A dermoscopic image of a skin lesion: 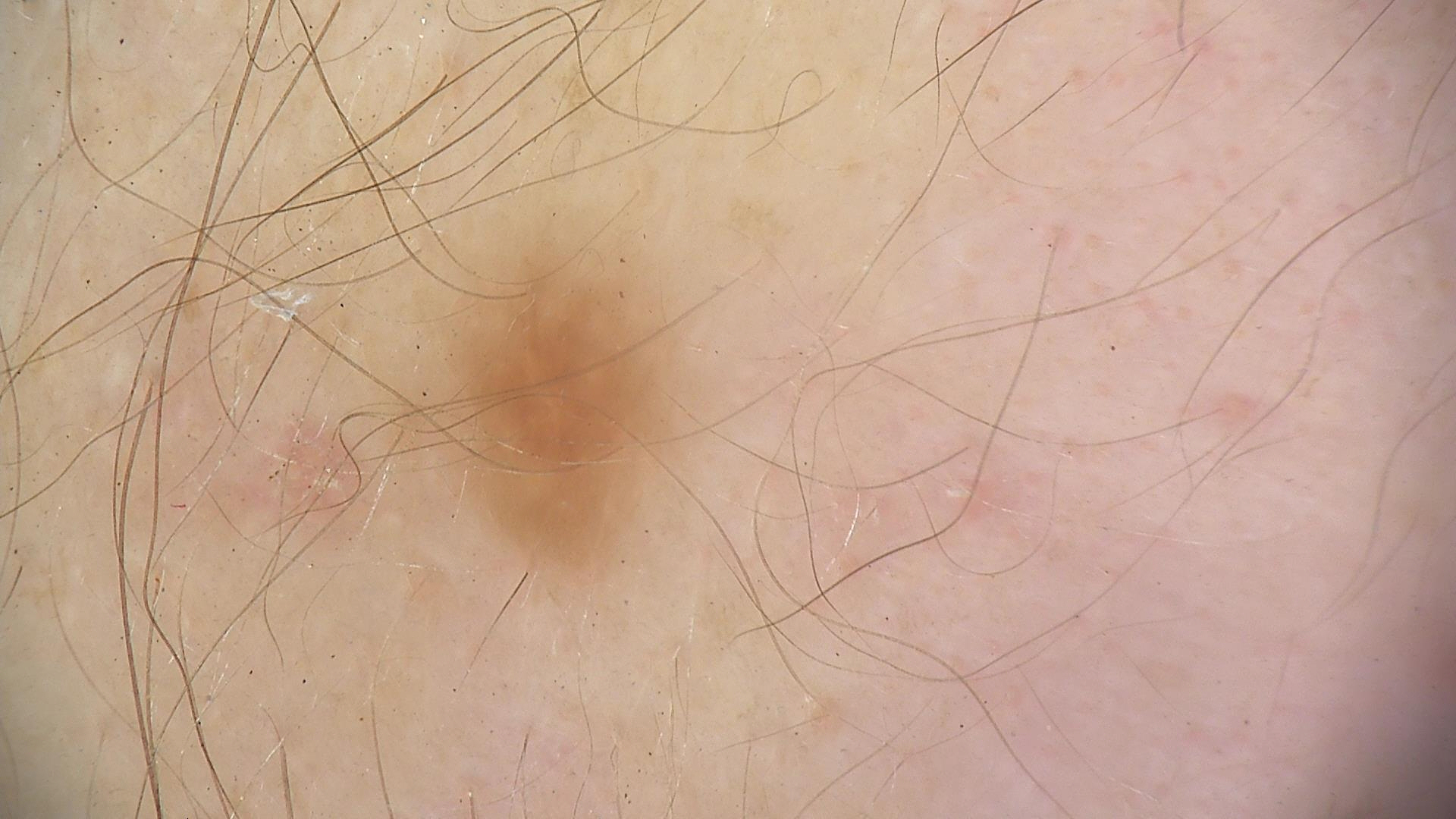Labeled as a dysplastic junctional nevus.